Dermoscopy of a skin lesion: 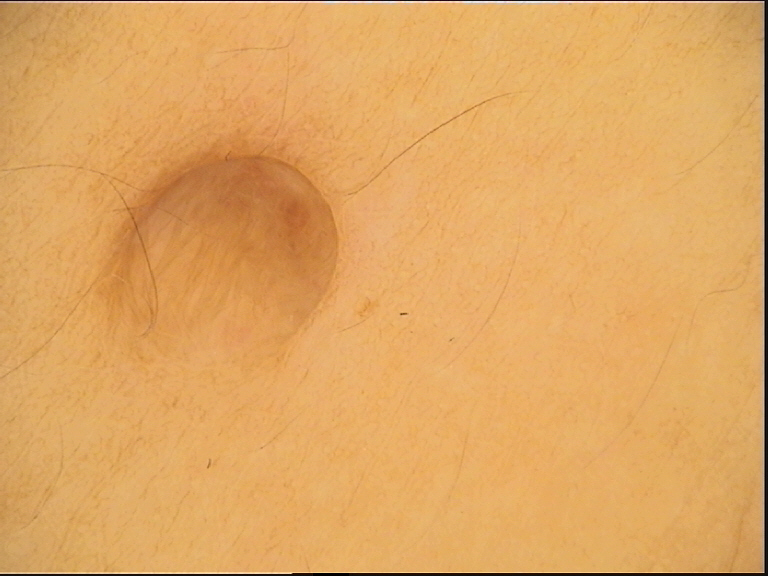Impression:
Diagnosed as a banal lesion — a dermal nevus.